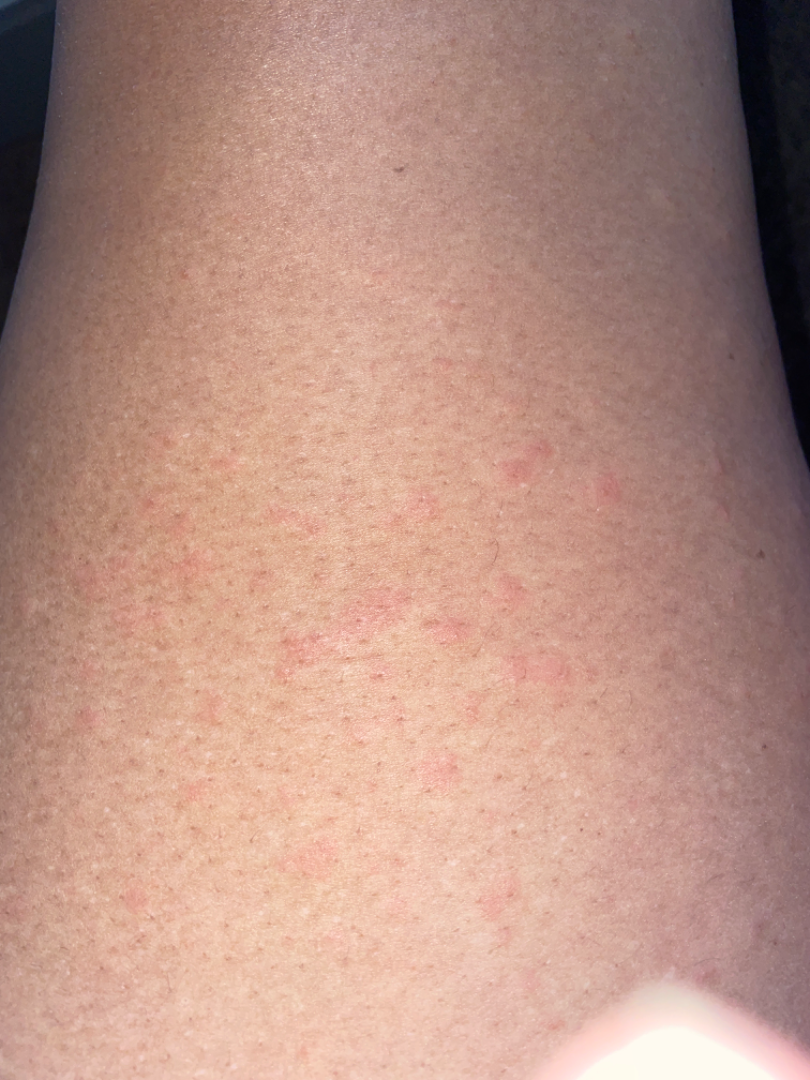The photograph was taken at an angle. The lesion involves the leg and arm. The favored diagnosis is Urticaria; a more distant consideration is Eczema; less likely is Allergic Contact Dermatitis.